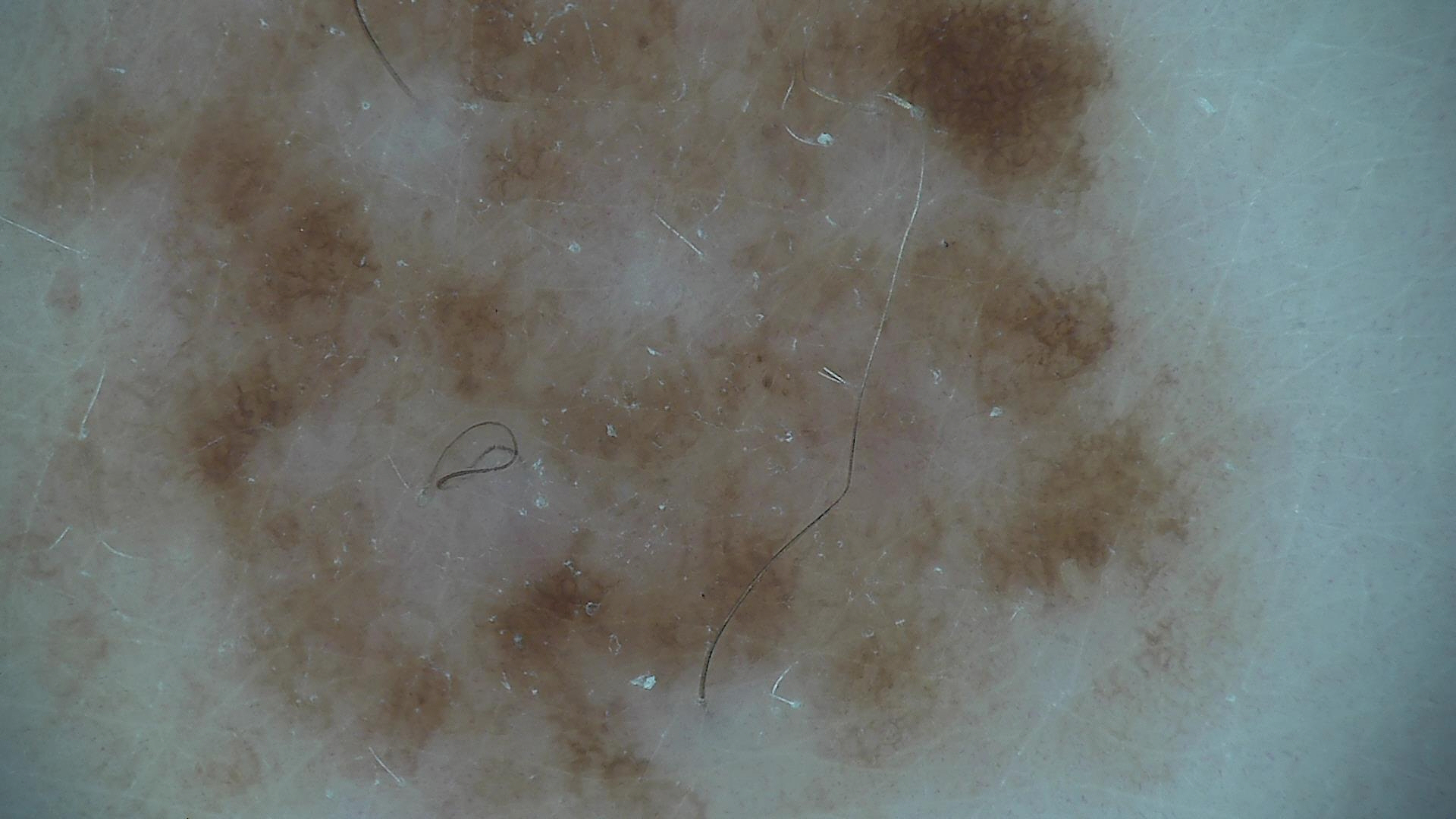- assessment · dysplastic junctional nevus (expert consensus)